A female subject age 50 · a moderate number of moles by the patient's own estimate · a macroscopic clinical photograph of a skin lesion · the referring clinician suspected melanoma · the patient says their skin reddens painfully with sun exposure.
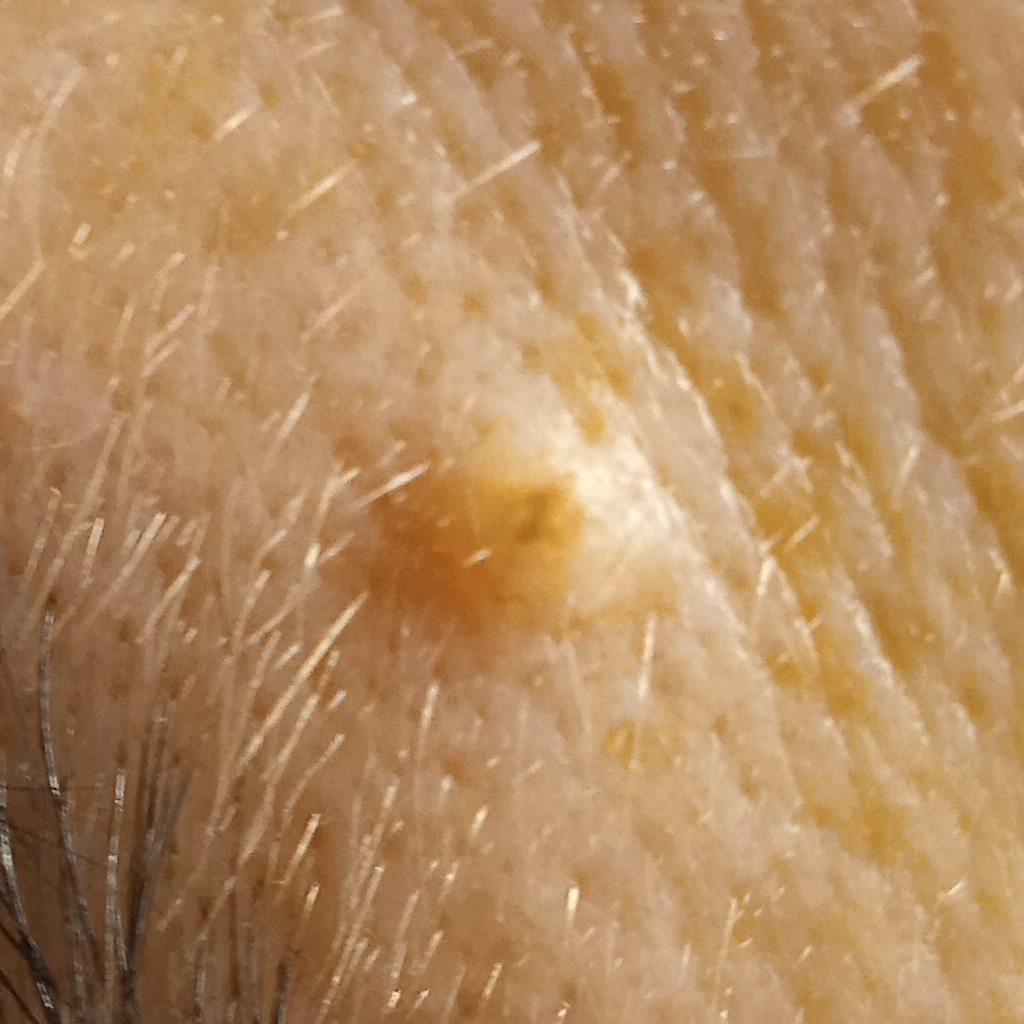| feature | finding |
|---|---|
| site | the face |
| size | 1.8 mm |
| diagnosis | melanocytic nevus (dermatologist consensus) |